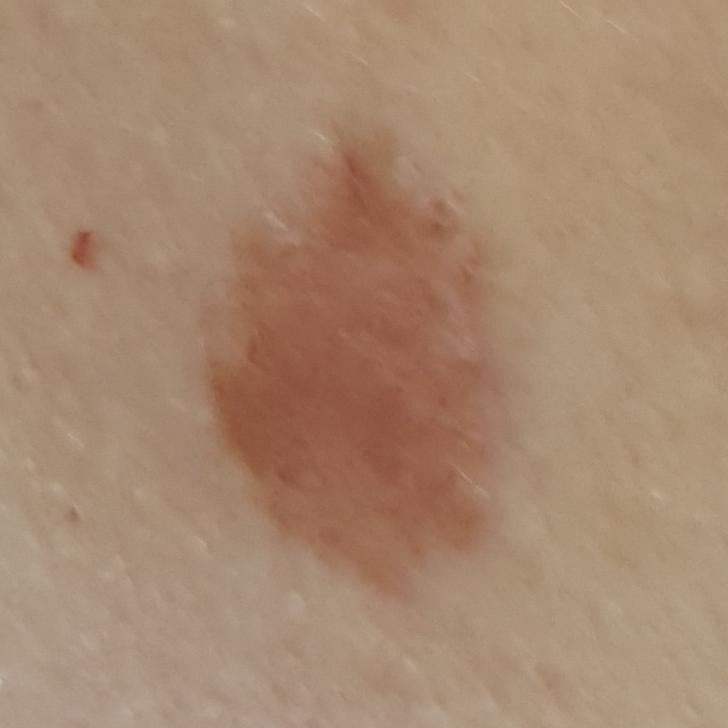A smartphone photograph of a skin lesion. A patient 22 years old. The lesion was found on the chest. Clinically diagnosed as a nevus.